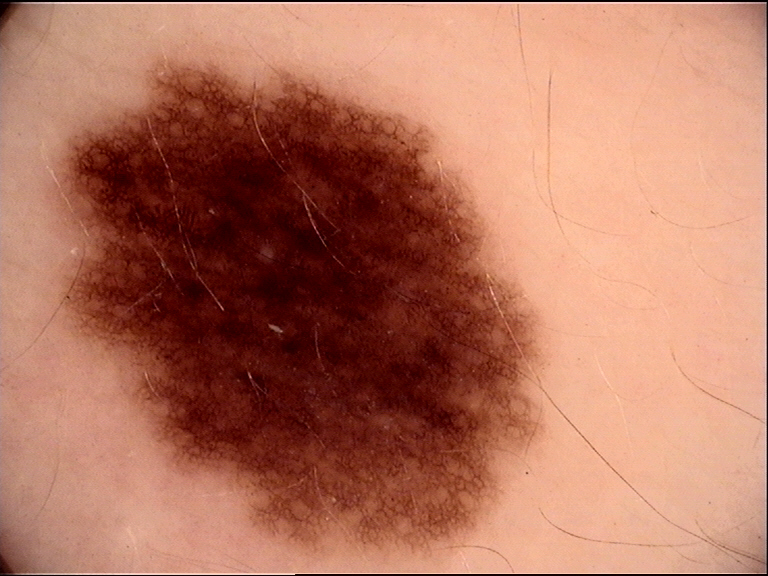{"diagnosis": {"name": "dysplastic junctional nevus", "code": "jd", "malignancy": "benign", "super_class": "melanocytic", "confirmation": "expert consensus"}}